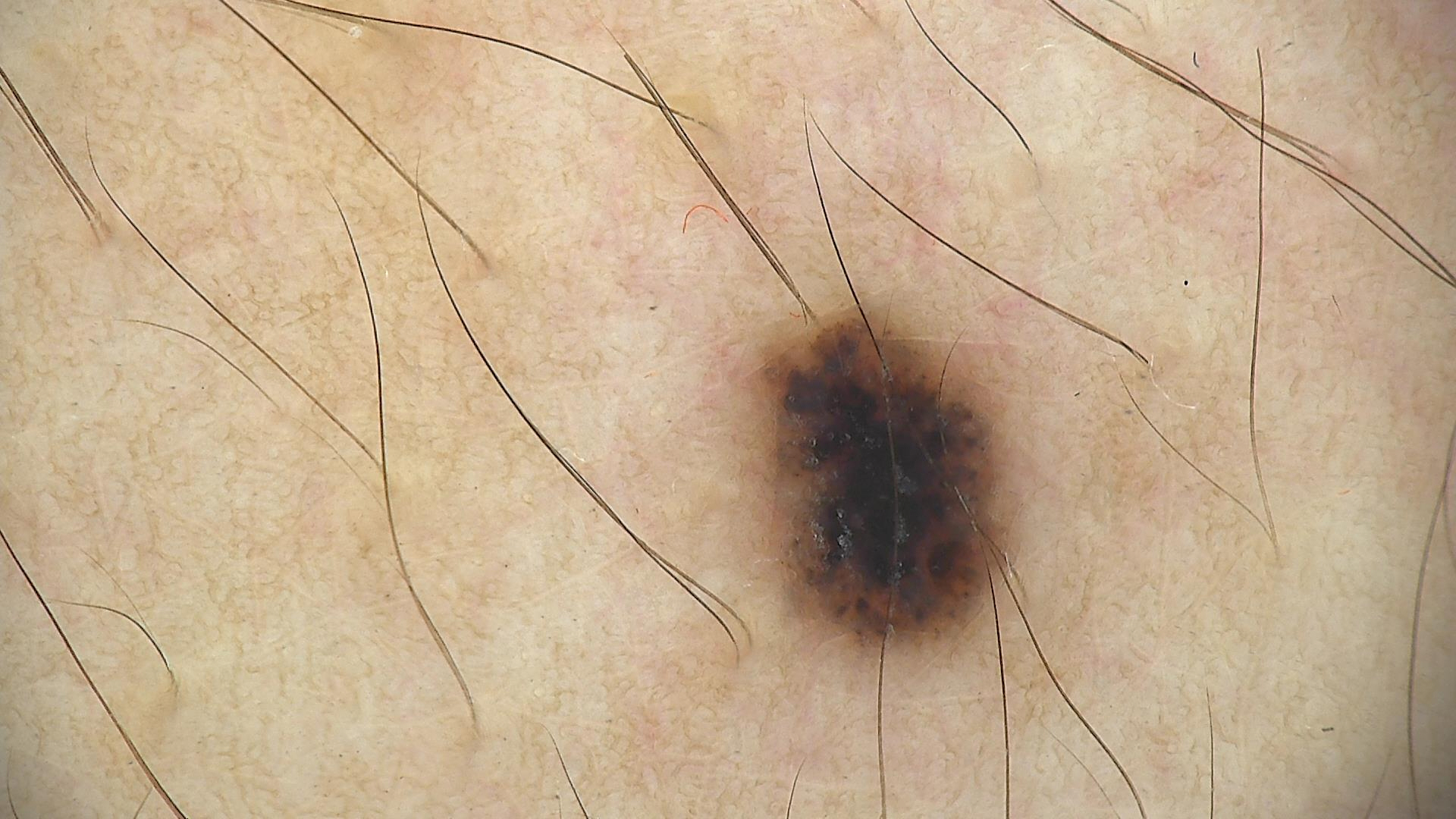{
  "image": "dermatoscopy",
  "diagnosis": {
    "name": "dysplastic compound nevus",
    "code": "cd",
    "malignancy": "benign",
    "super_class": "melanocytic",
    "confirmation": "expert consensus"
  }
}